A dermoscopic photograph of a skin lesion.
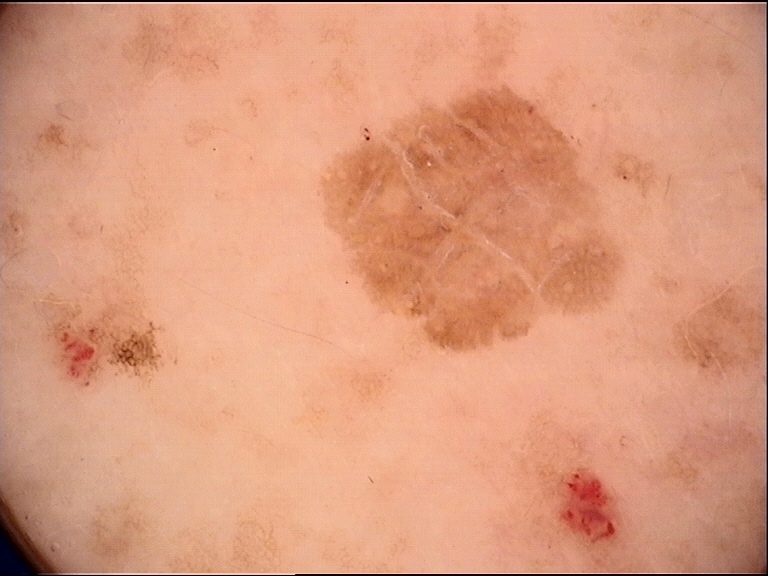Summary:
This is a keratinocytic lesion.
Impression:
Labeled as a benign lesion — a seborrheic keratosis.